This is a close-up image:
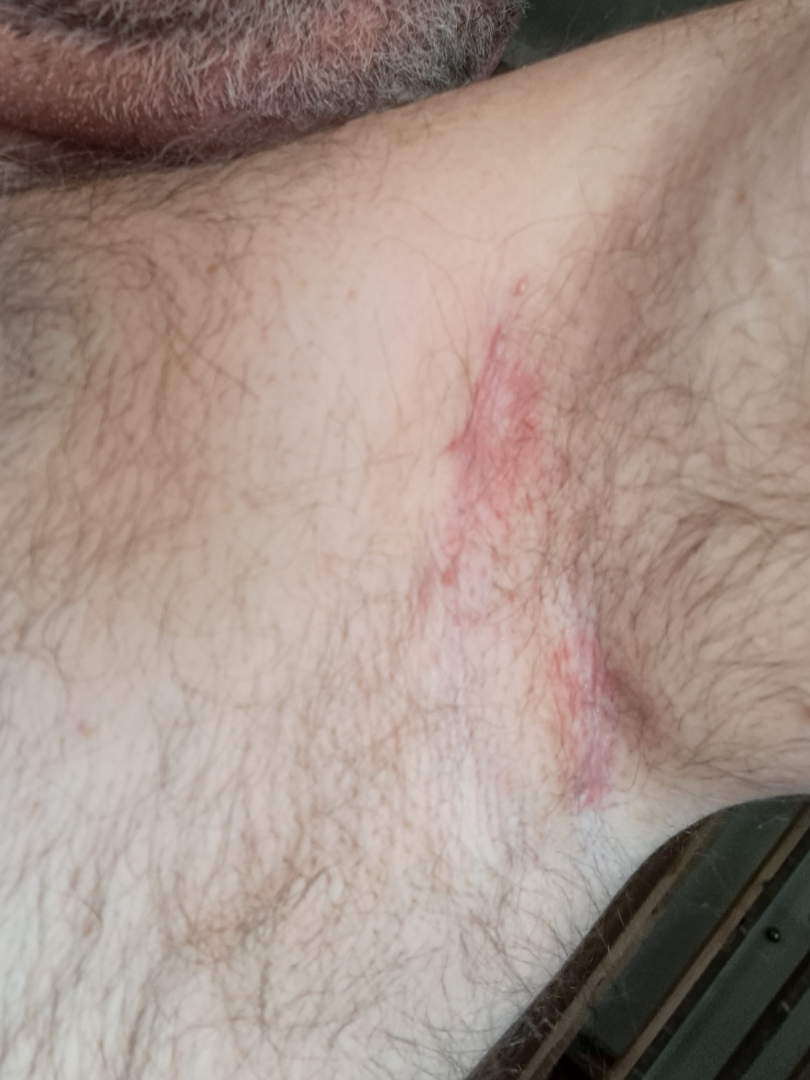Q: How does the patient describe it?
A: a rash
Q: What is the patient's skin tone?
A: Fitzpatrick phototype II; human graders estimated Monk Skin Tone 2 (US pool) or 3 (India pool)
Q: Texture?
A: raised or bumpy
Q: Reported symptoms?
A: bothersome appearance
Q: Duration?
A: one to four weeks
Q: What conditions are considered?
A: the impression was split between Intertrigo, Psoriasis and Seborrheic Dermatitis